A dermoscopic image of a skin lesion — 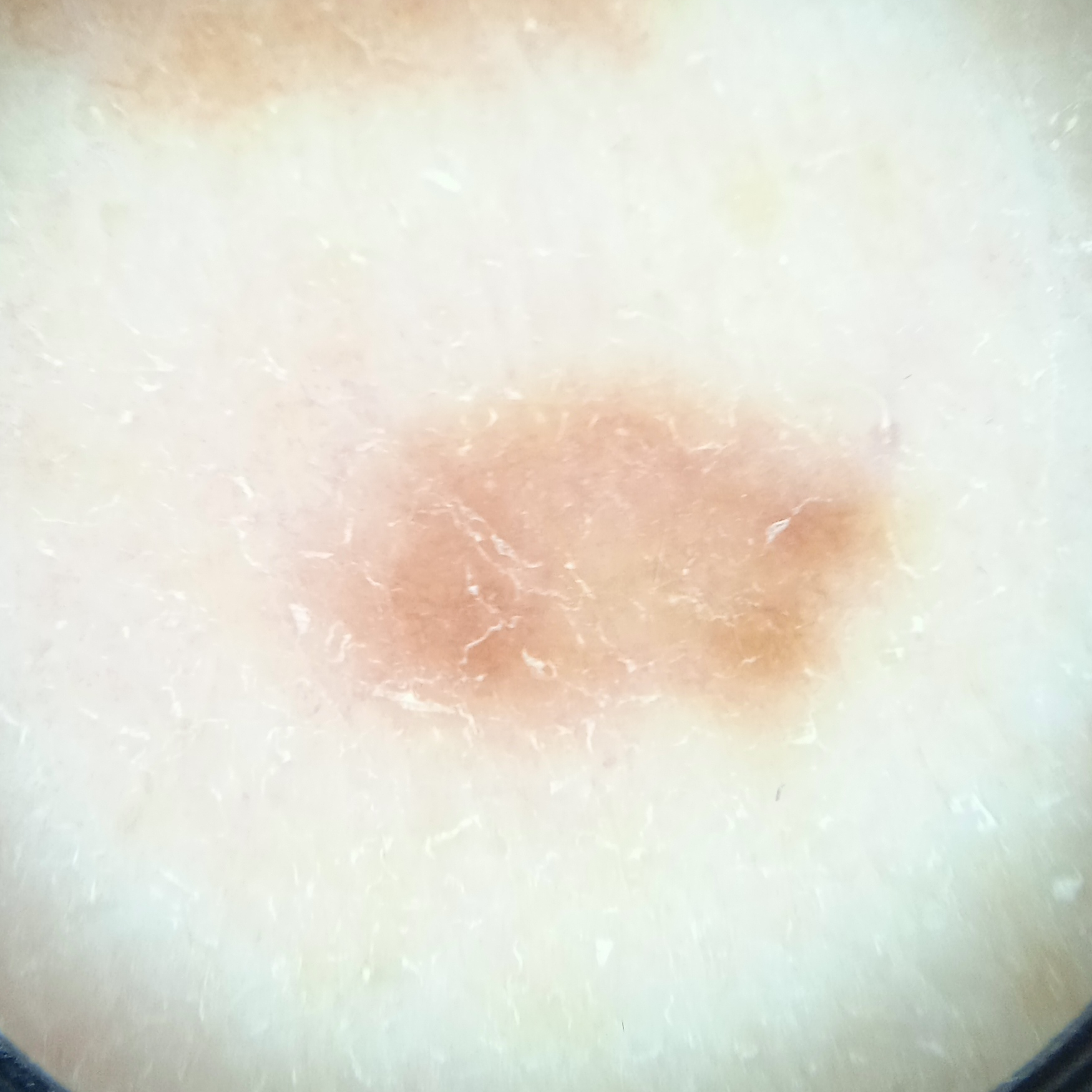Clinical context:
The lesion is located on the back. The lesion is about 8.6 mm across.
Conclusion:
Dermatologist review favored an atypical (dysplastic) nevus.